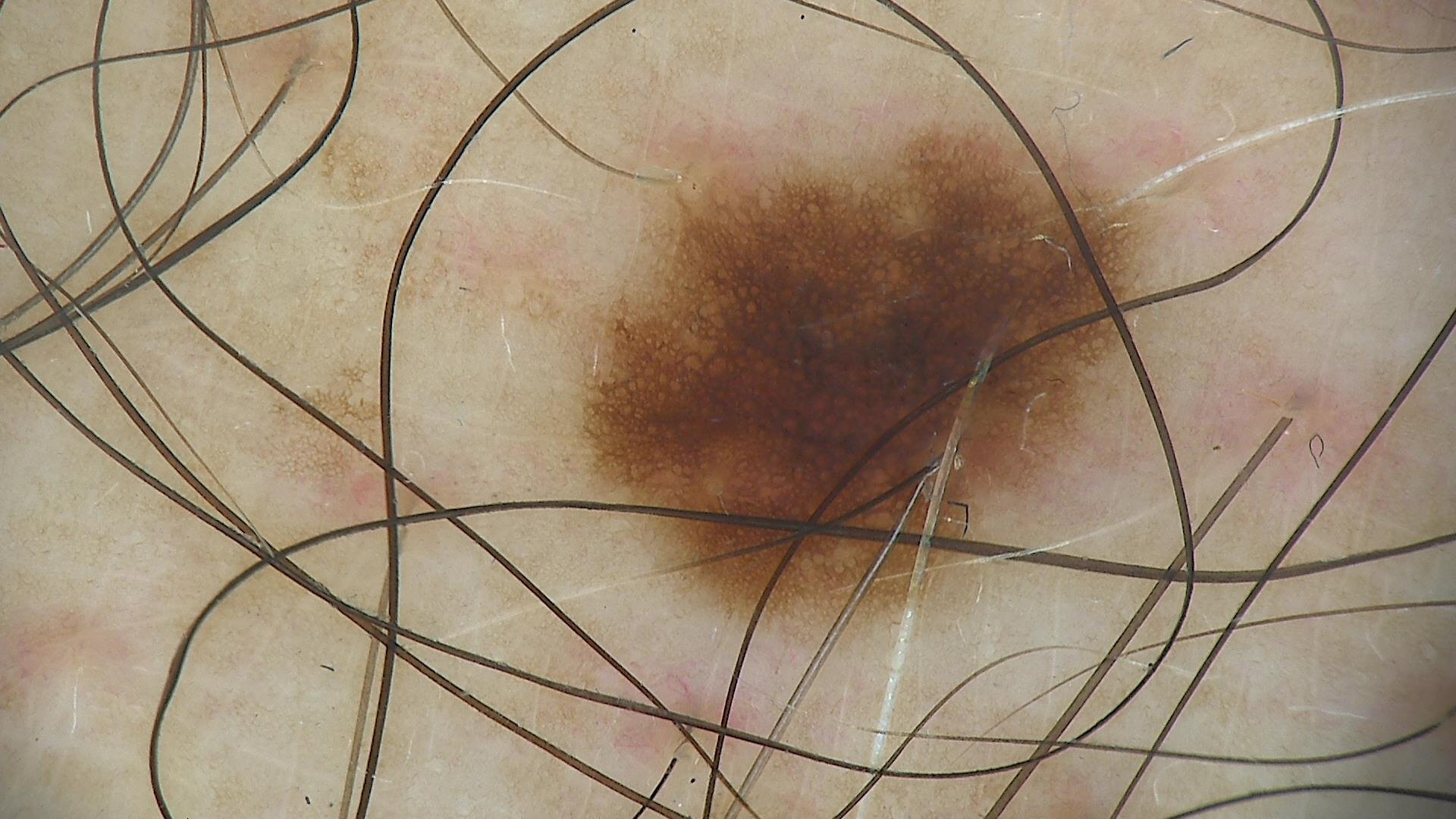Consistent with a dysplastic junctional nevus.